The back of the torso is involved. The photograph was taken at a distance: 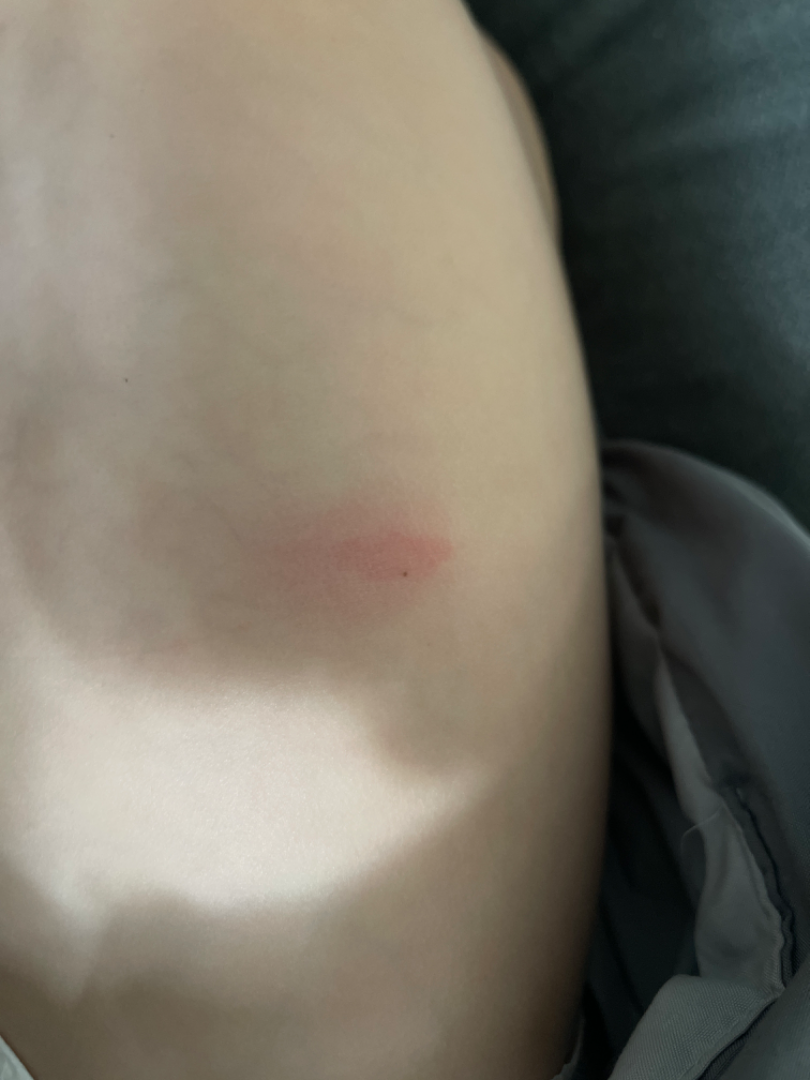assessment=not assessable.